A dermoscopy image of a single skin lesion.
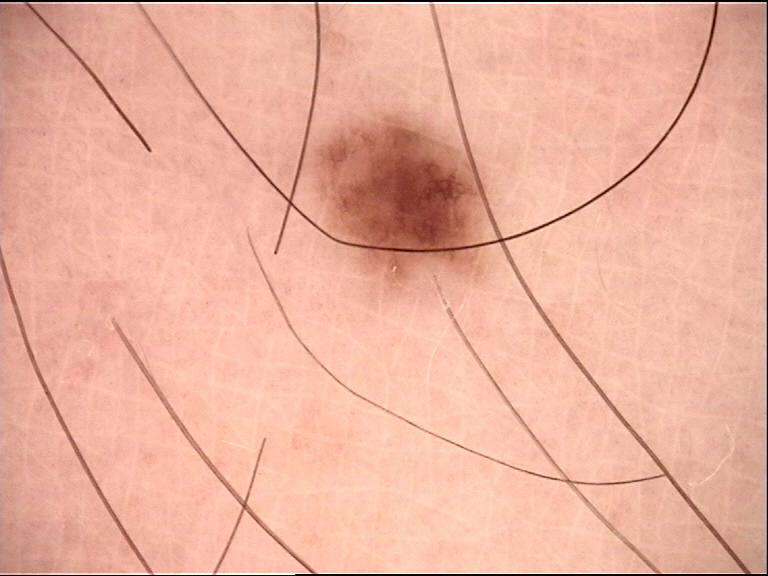assessment — dysplastic junctional nevus (expert consensus)